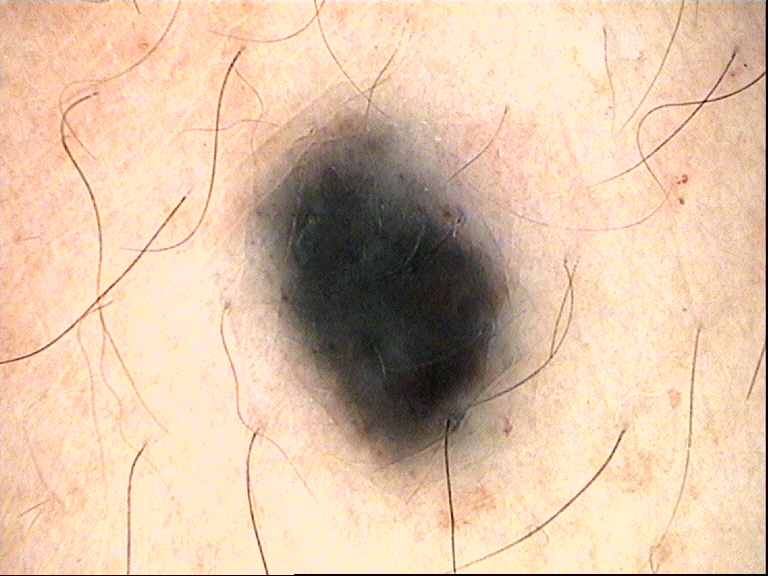This is a dermal, banal lesion. The diagnosis was a blue nevus.